A dermoscopic close-up of a skin lesion.
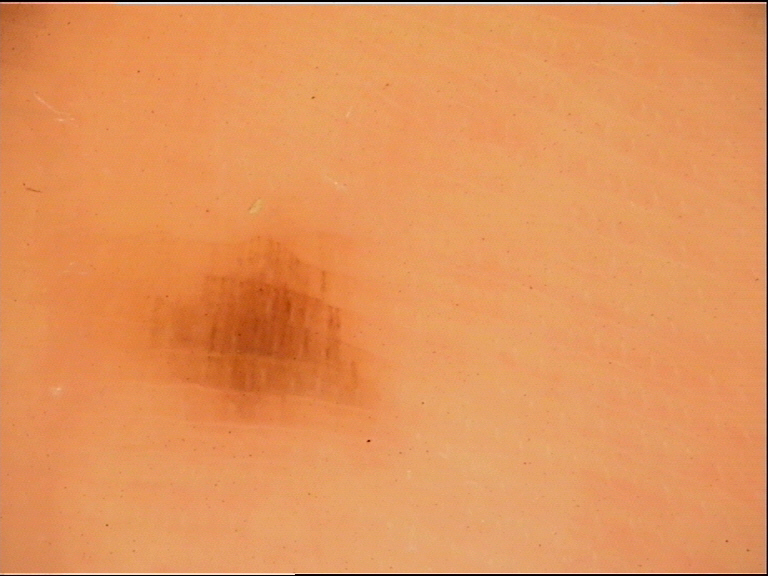Q: What is the diagnosis?
A: acral junctional nevus (expert consensus)